A dermatoscopic image of a skin lesion · a male patient aged around 70 — 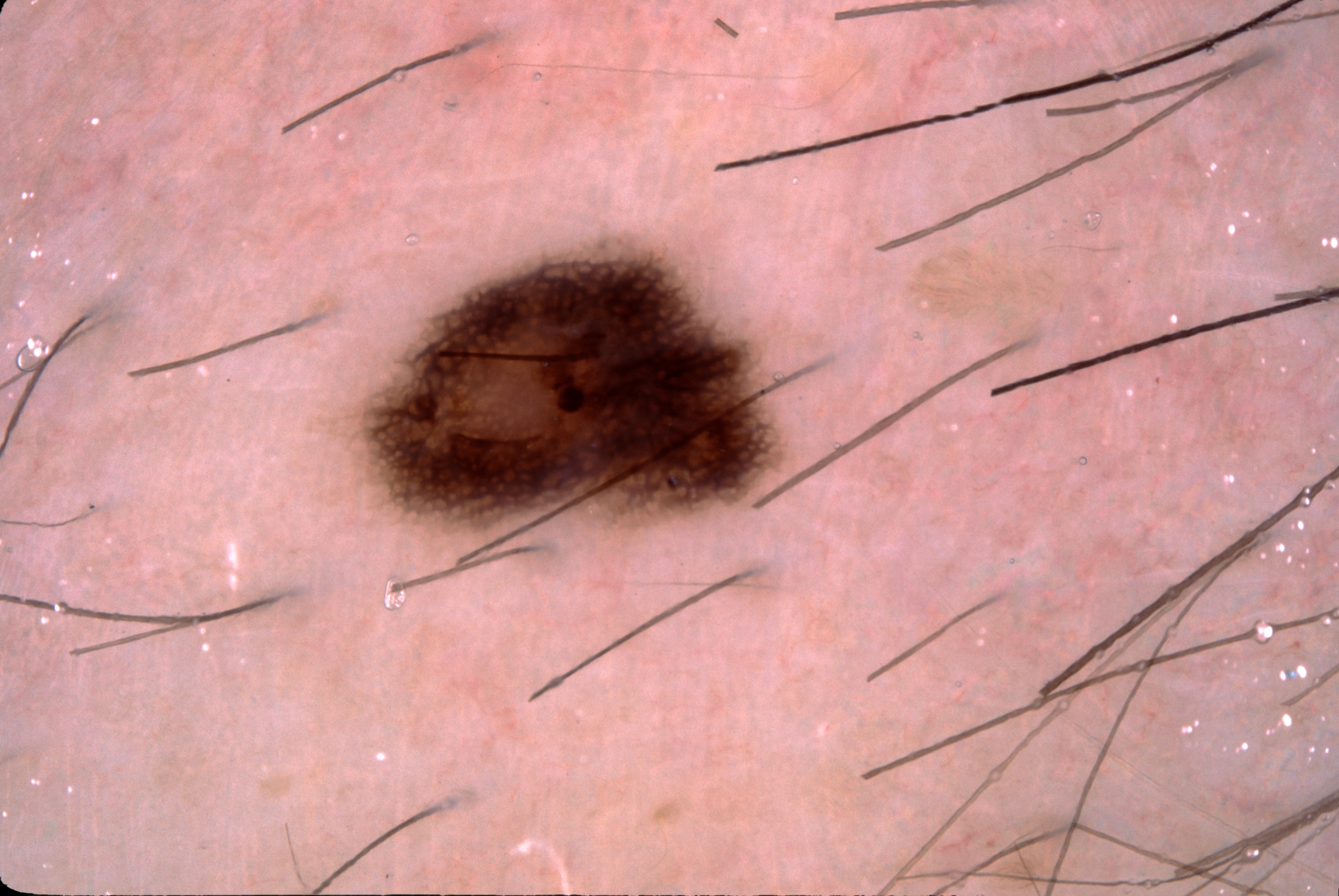The lesion spans bbox=[366, 252, 774, 532].
The lesion takes up about 7% of the image.
On dermoscopy, the lesion shows pigment network.
The diagnostic assessment was a melanocytic nevus.